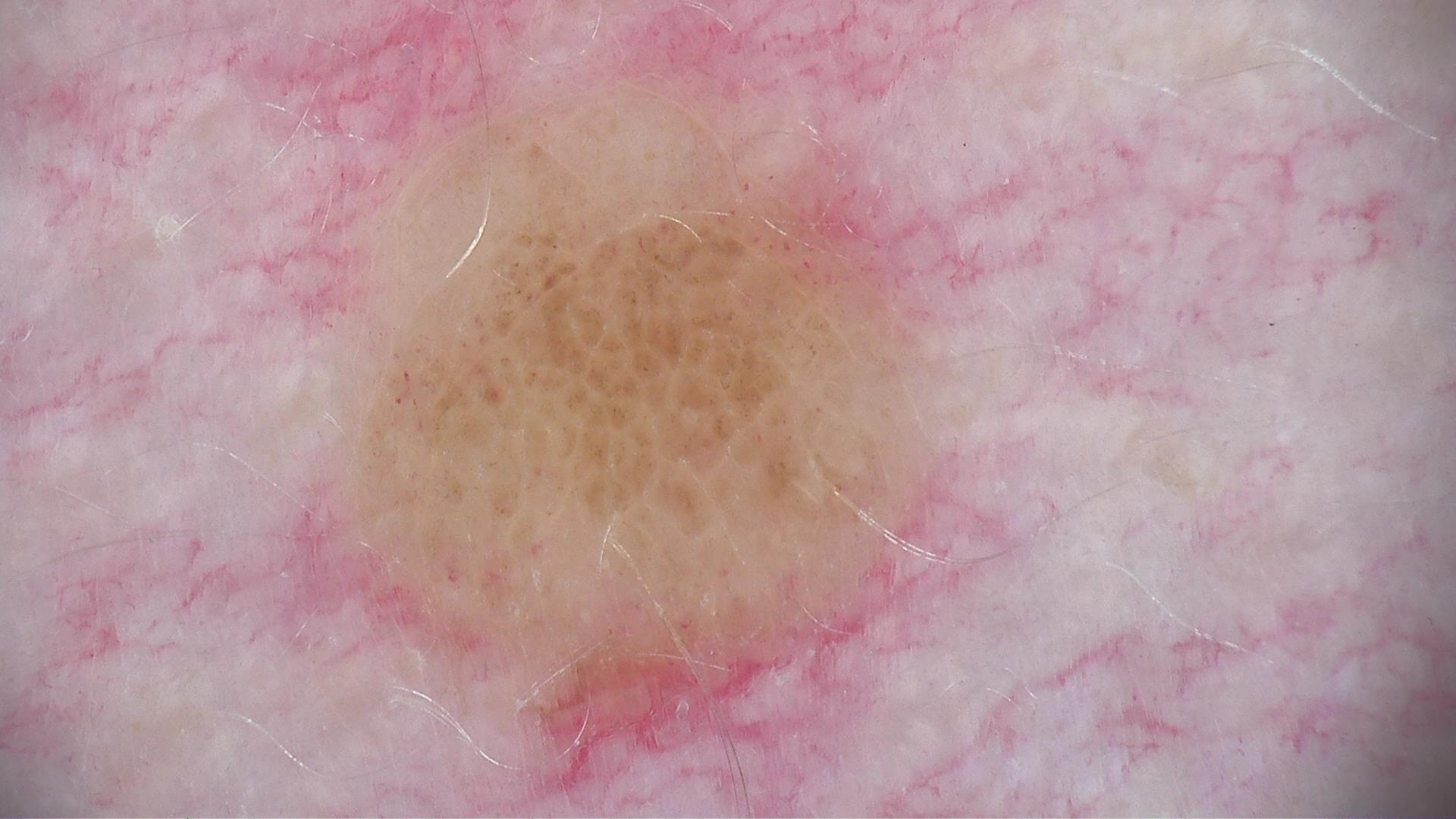diagnosis: dermal nevus (expert consensus).